A skin lesion imaged with a dermatoscope: 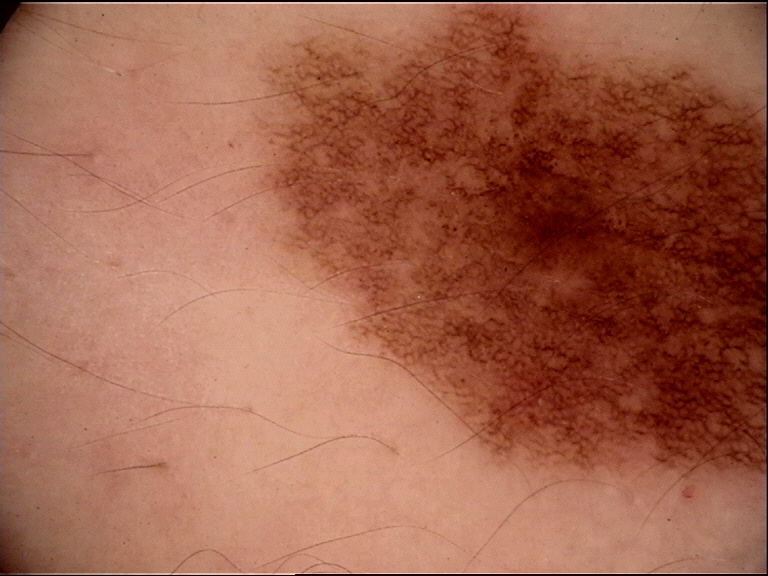The diagnosis was a benign lesion — a dysplastic junctional nevus.